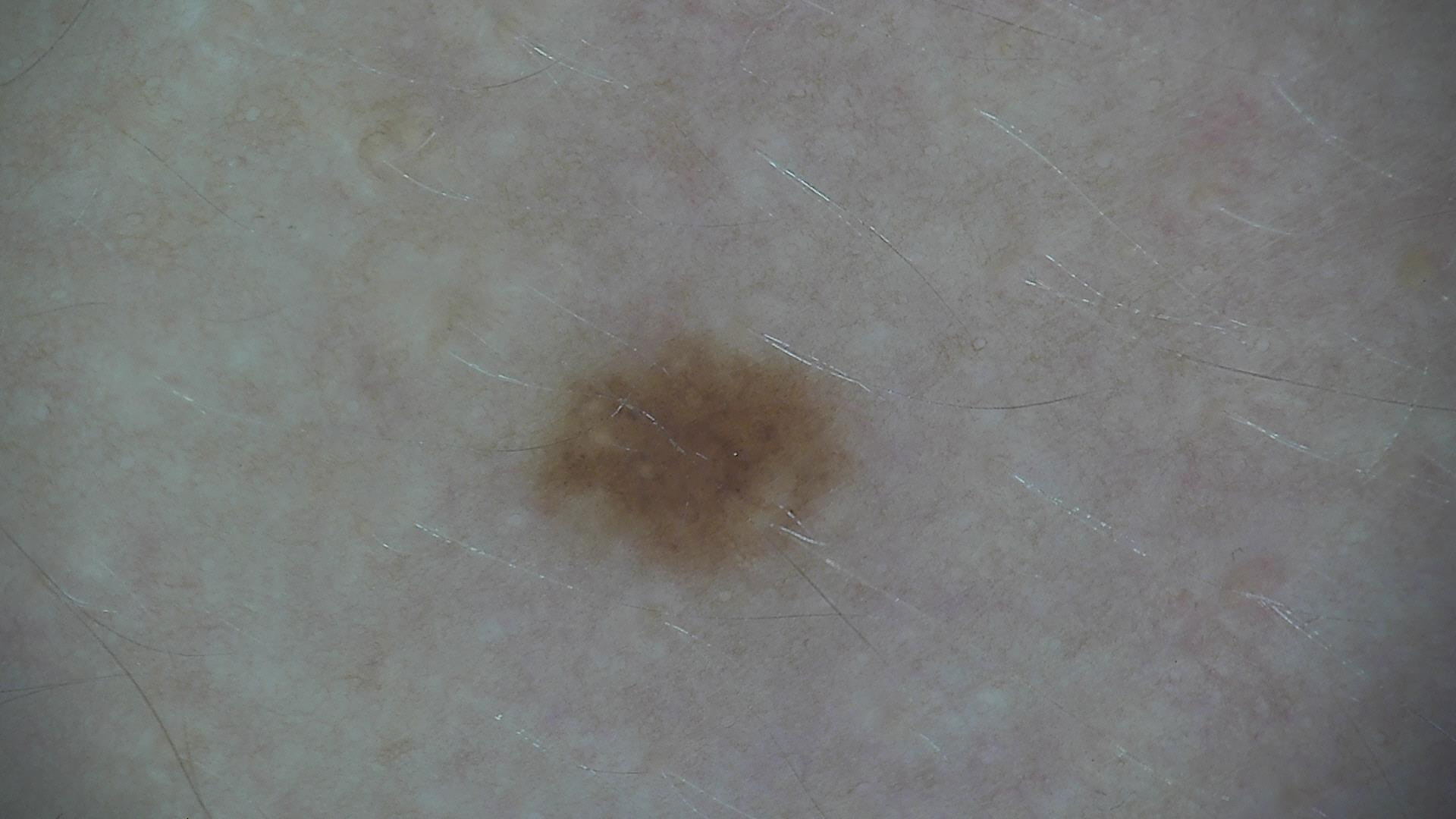  diagnosis:
    name: dysplastic junctional nevus
    code: jd
    malignancy: benign
    super_class: melanocytic
    confirmation: expert consensus